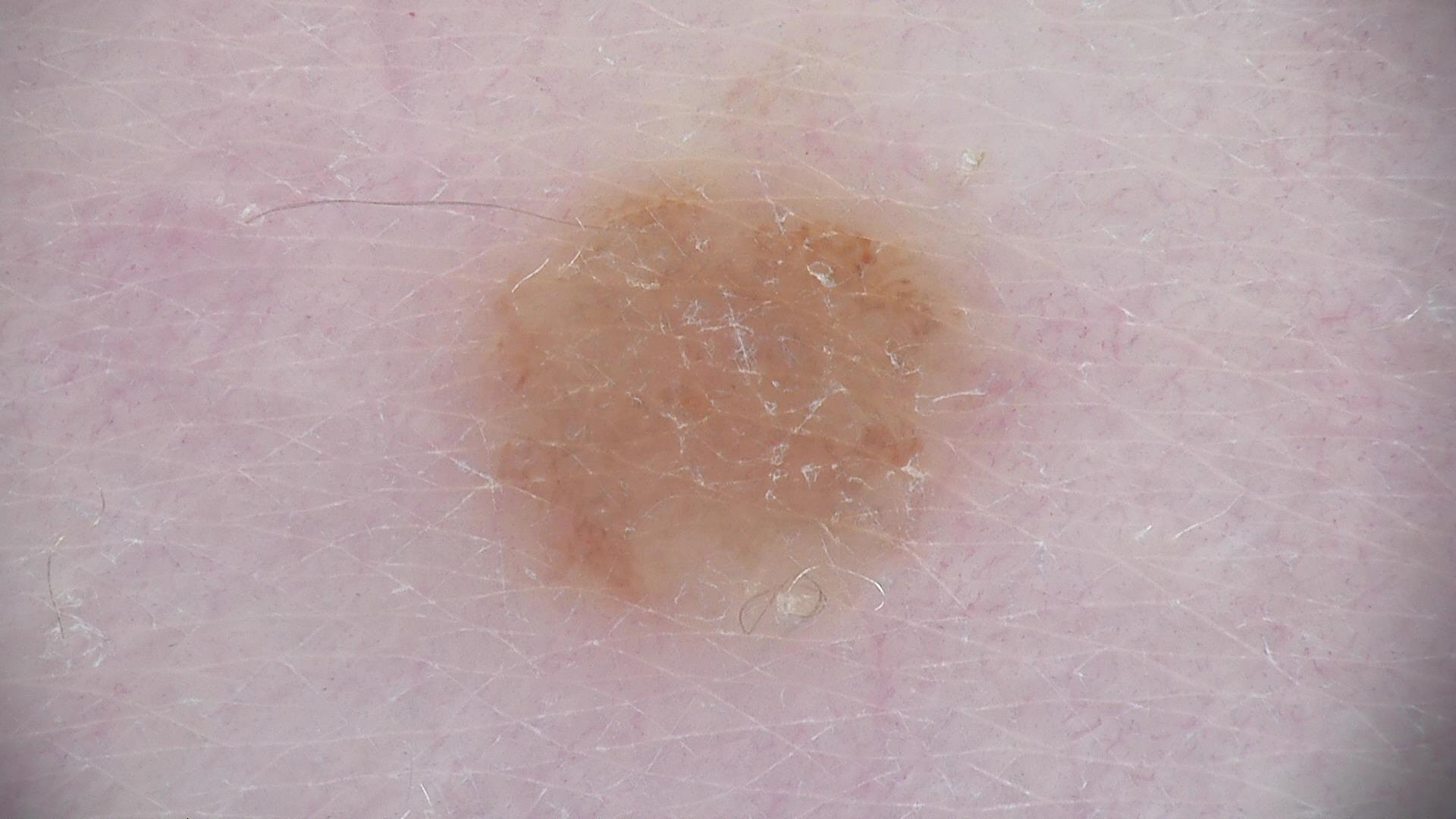The diagnosis was a banal lesion — a dermal nevus.